This is a close-up image · the lesion involves the head or neck · the patient is female — 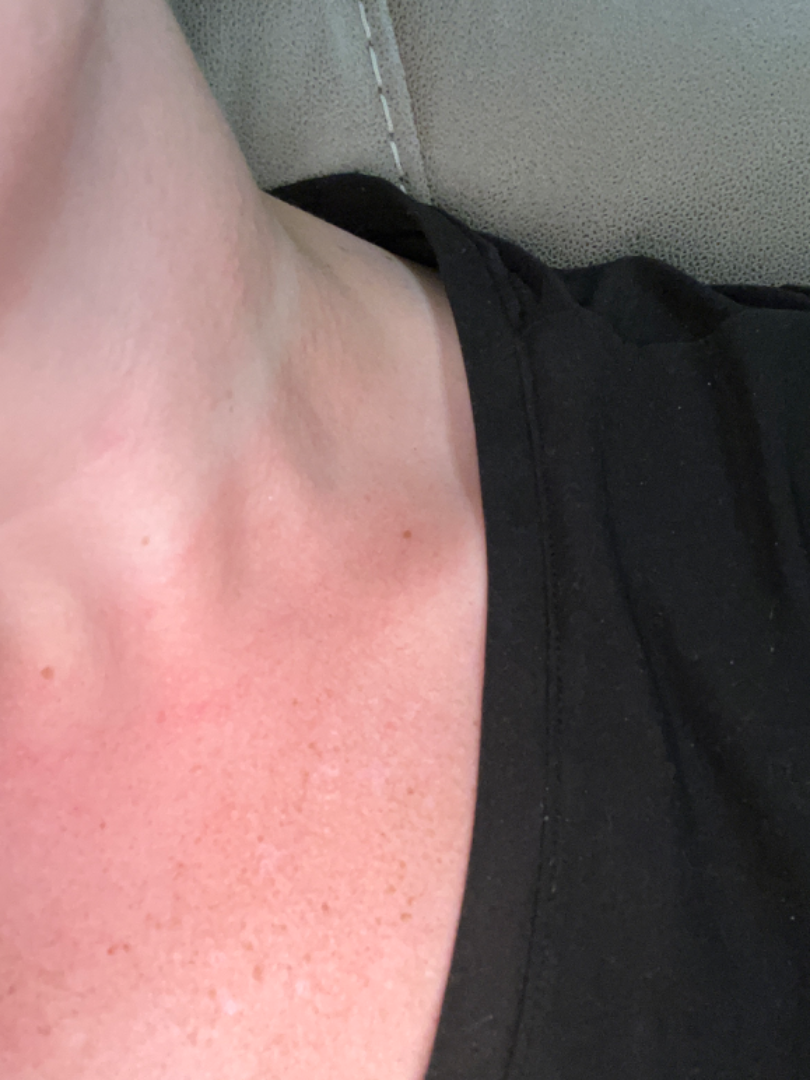On teledermatology review: most consistent with Photodermatitis; with consideration of Hypersensitivity.